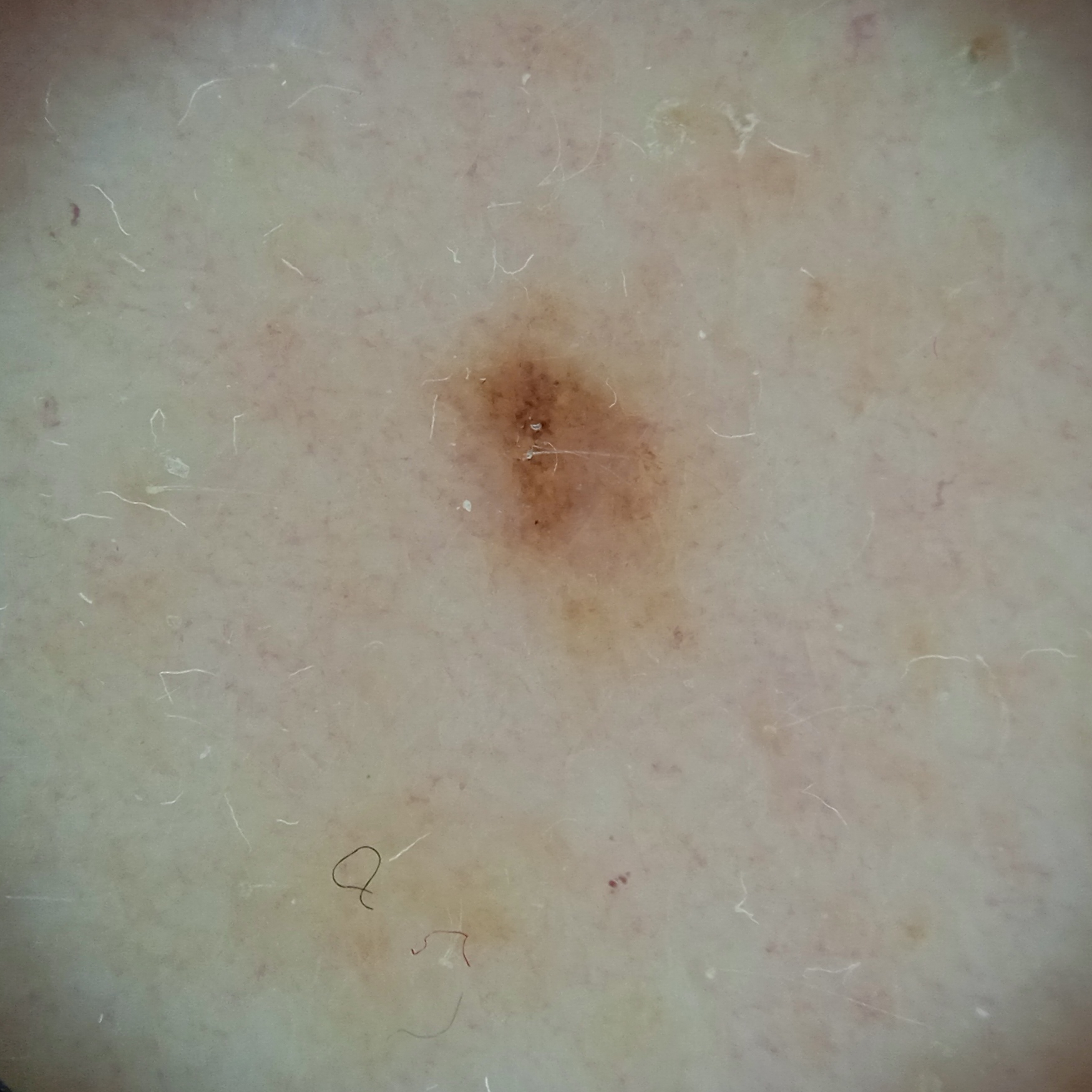Collected as part of a research study, without a referral diagnosis.
The patient describes having a moderate number of moles.
A dermoscopic image of a skin lesion.
The patient says their skin reddens painfully with sun exposure.
A female patient age 55.
Dermatologist review favored a melanocytic nevus.